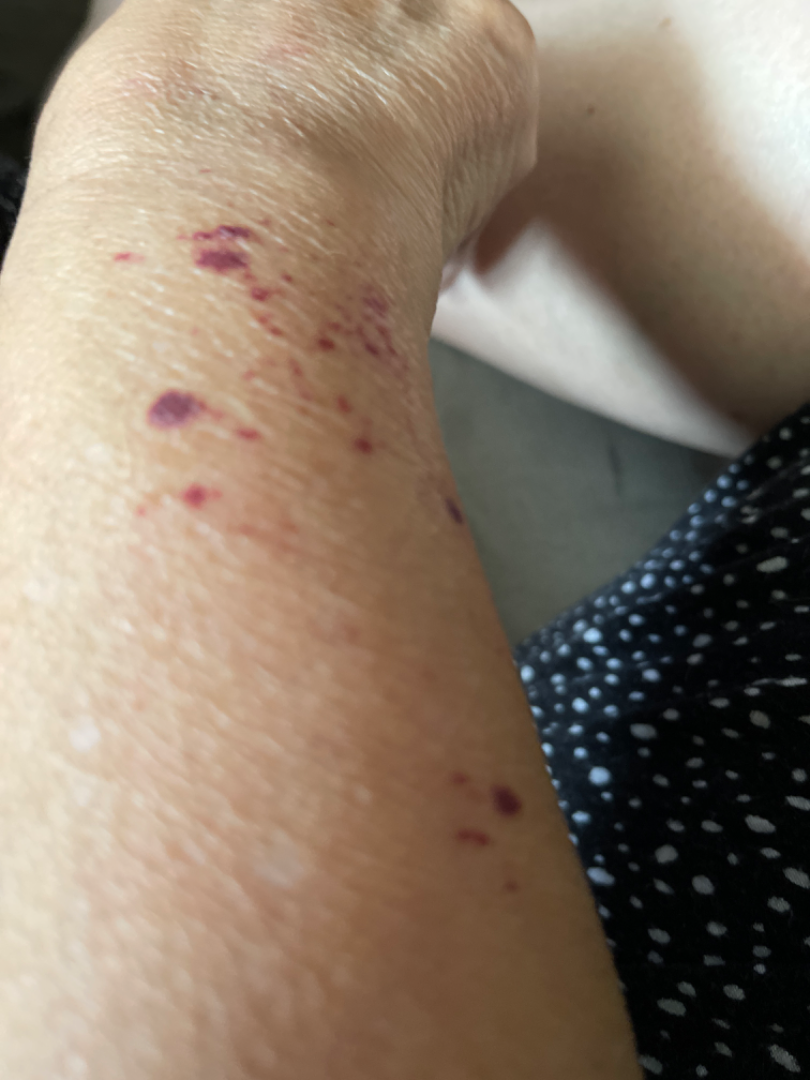An image taken at an angle. The patient is 50–59, female. The back of the hand and arm are involved. On remote review of the image, ecchymoses (primary).